Close-up view. Located on the arm.
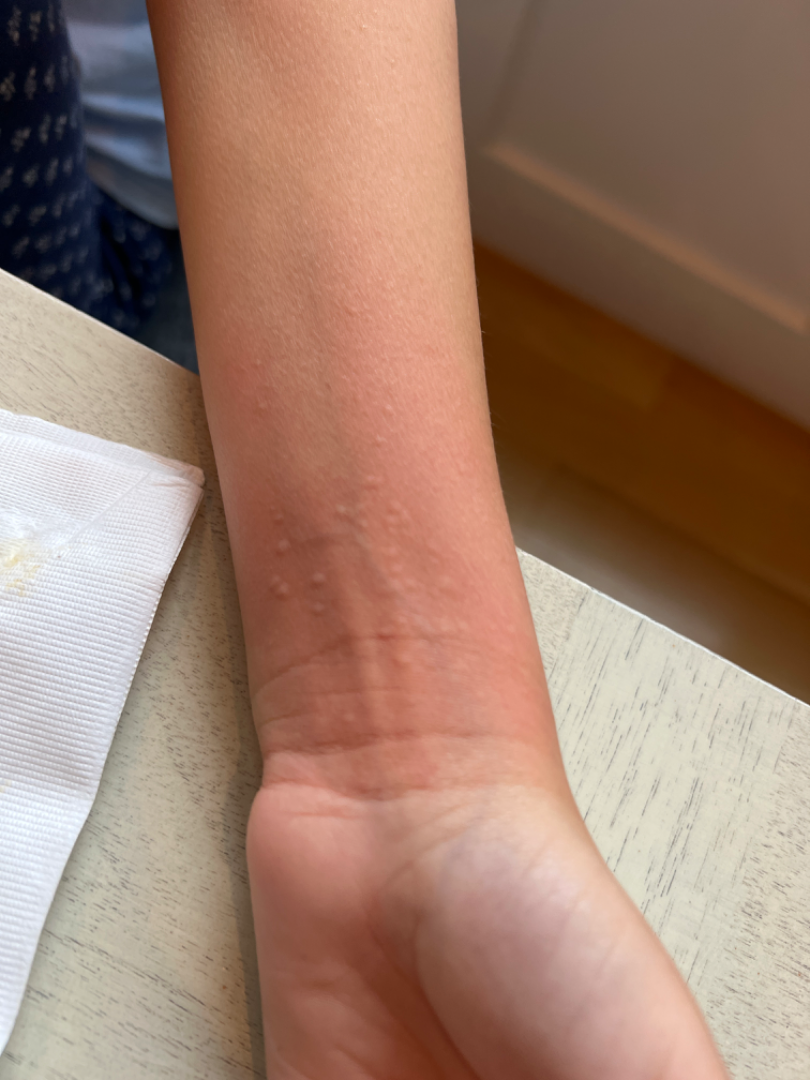Background:
The patient reported no systemic symptoms. The patient considered this a rash. The lesion is described as raised or bumpy. The condition has been present for about one day.
Findings:
On remote dermatologist review: the favored diagnosis is Urticaria.